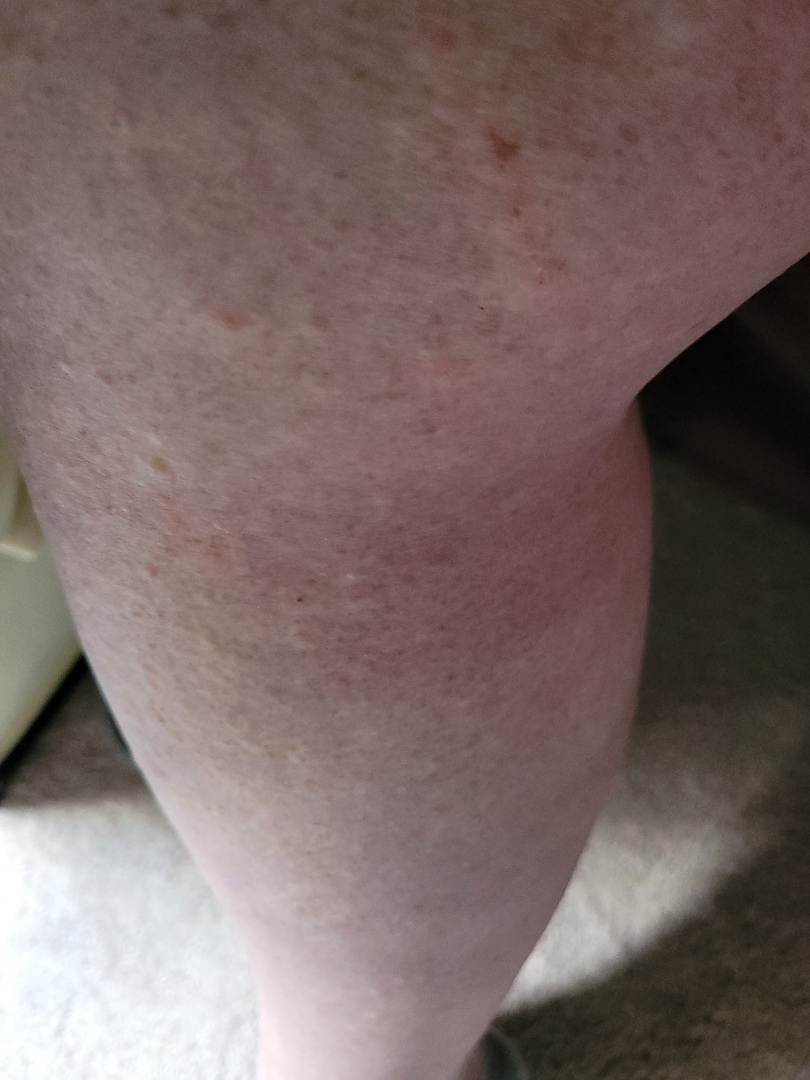clinical impression — the favored diagnosis is Eczema.